A dermoscopic close-up of a skin lesion.
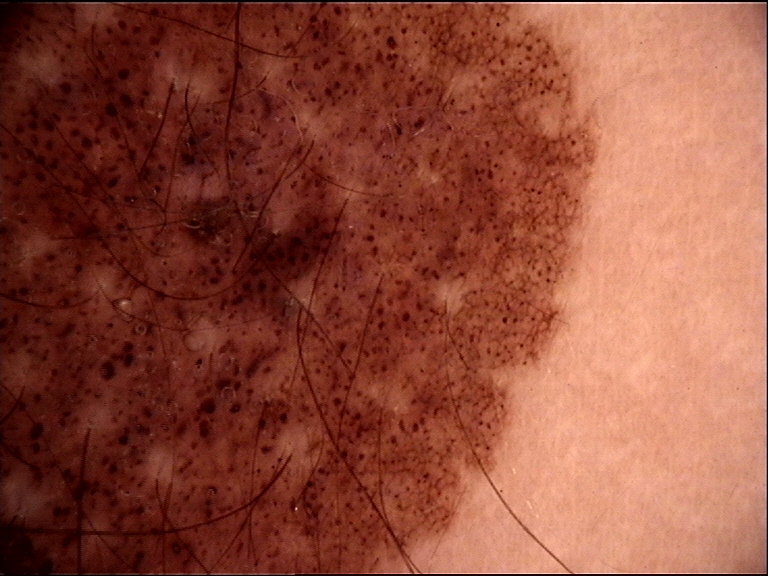Conclusion: Diagnosed as a banal lesion — a congenital compound nevus.